The photograph is a close-up of the affected area:
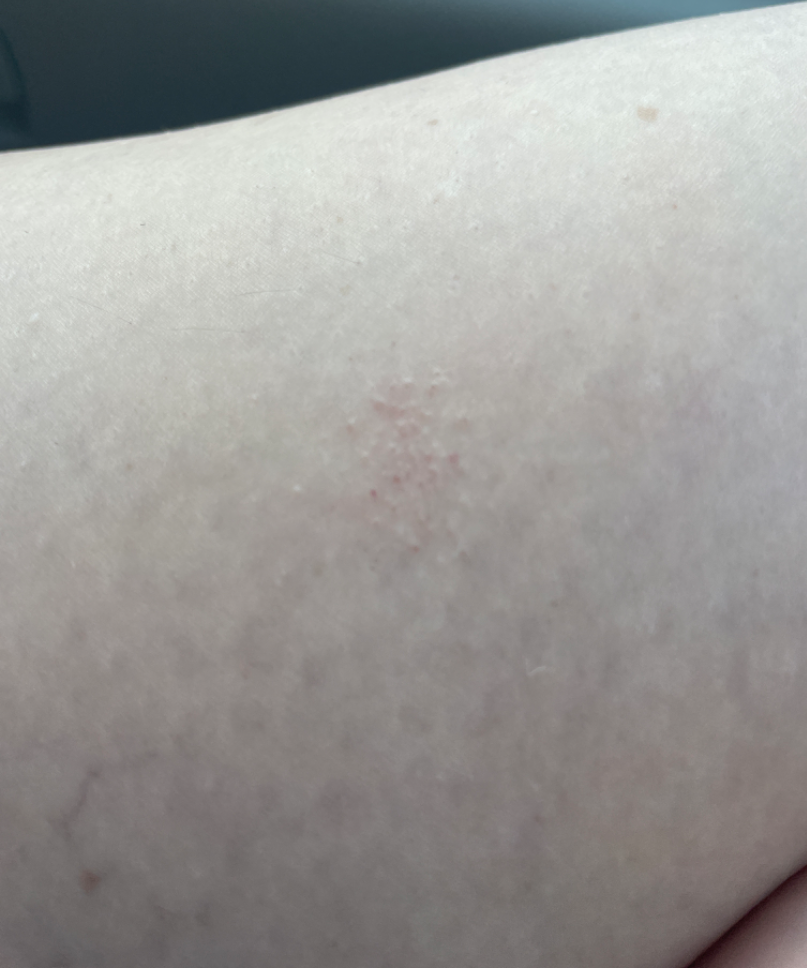Review: Most consistent with Lichen spinulosus; with consideration of Eczema.